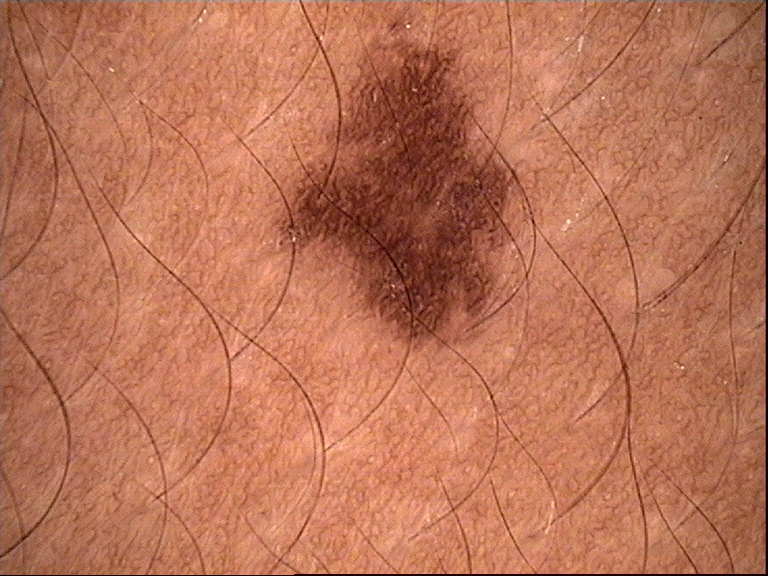The diagnosis was a dysplastic junctional nevus.